A clinical photograph showing a skin lesion. A subject in their 70s:
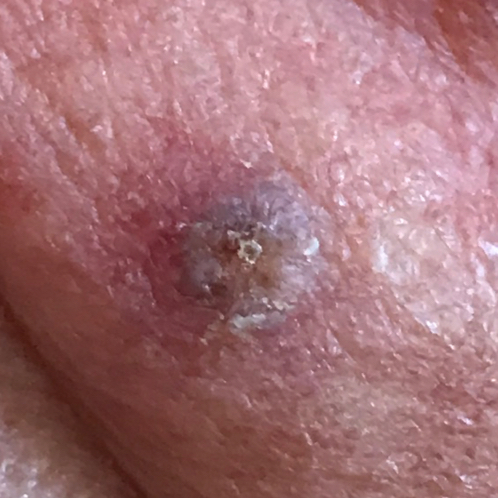The lesion is on the face. Expert review favored a seborrheic keratosis.